The affected area is the leg. This image was taken at an angle. The contributor is a female aged 50–59 — 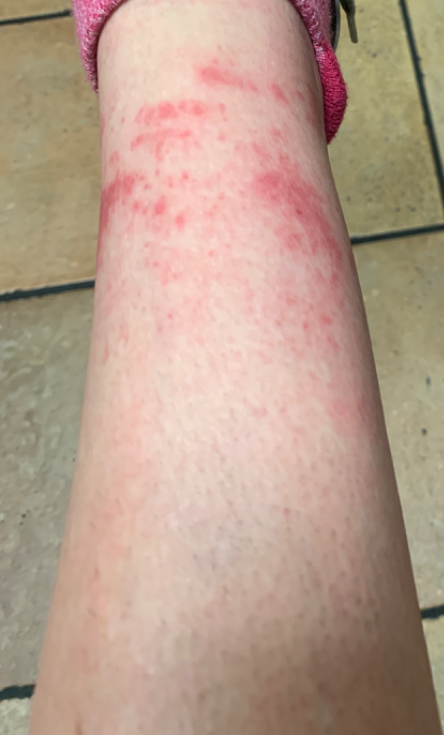– patient's own categorization · a rash
– constitutional symptoms · fever and mouth sores
– lesion texture · flat
– onset · about one day
– assessment · the differential is split between Stasis Dermatitis; Acute dermatitis, NOS; and Leukocytoclastic Vasculitis